This image was taken at an angle.
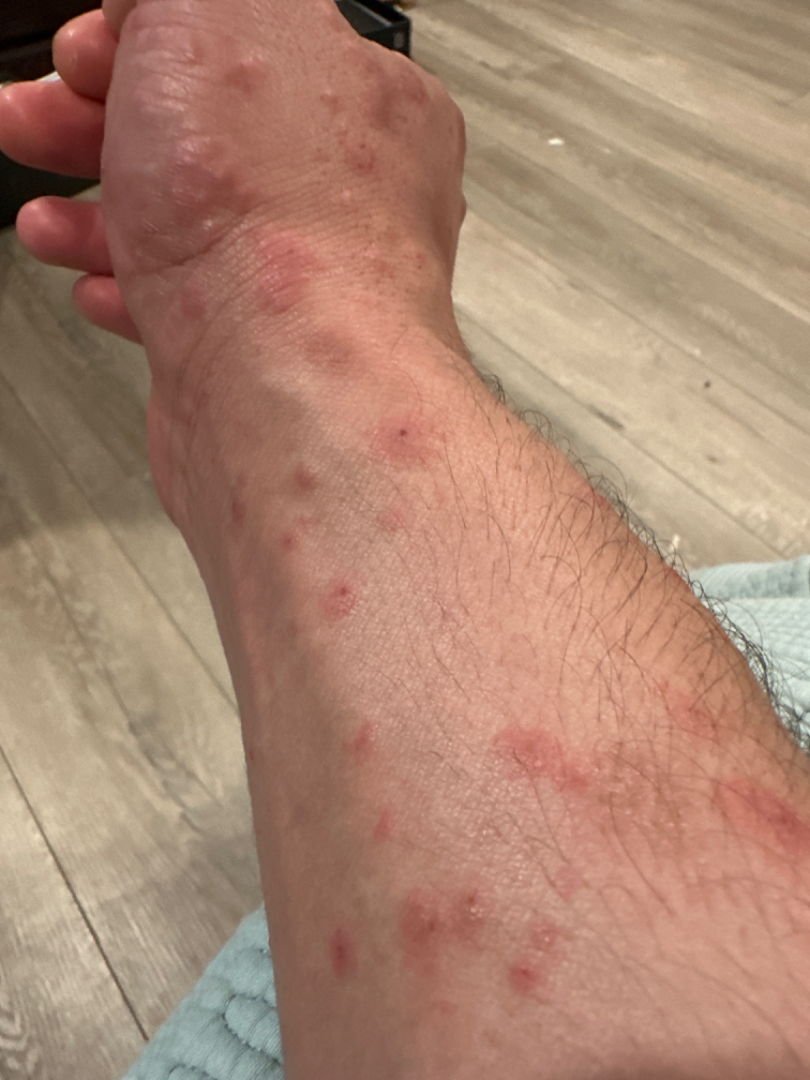- differential diagnosis: Insect Bite (most likely); Allergic Contact Dermatitis (possible)